A dermoscopic photograph of a skin lesion. The chart records melanoma in a first-degree relative. A female subject in their mid-60s. The patient was assessed as Fitzpatrick phototype II — 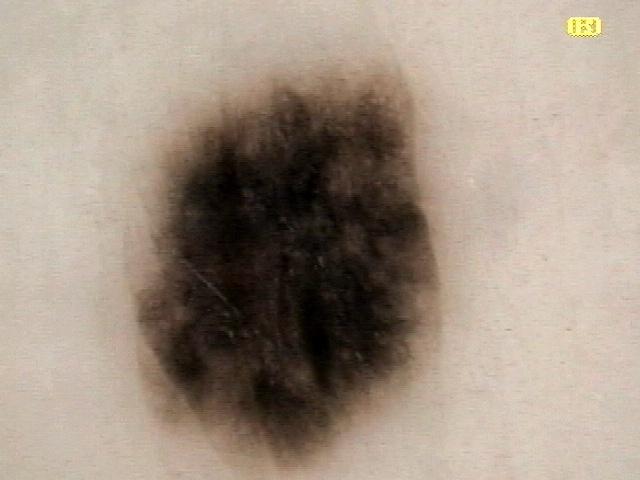| field | value |
|---|---|
| anatomic site | a lower extremity |
| diagnosis | Nevus (biopsy-proven) |